A male subject roughly 85 years of age or older, a dermoscopy image of a single skin lesion.
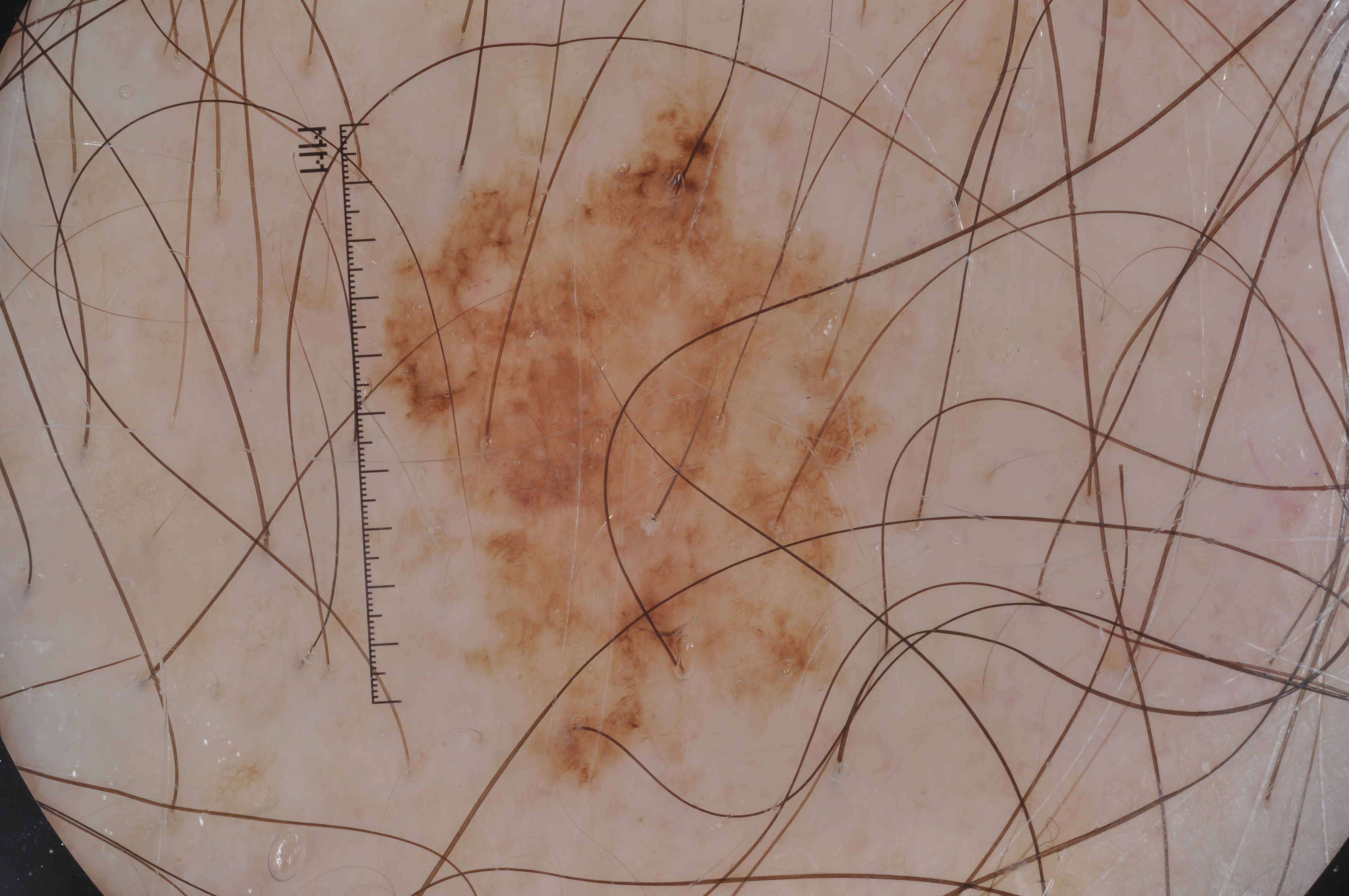<record>
  <dermoscopic_features>
    <present>pigment network</present>
    <absent>negative network, milia-like cysts, streaks</absent>
  </dermoscopic_features>
  <lesion_location>
    <bbox_xyxy>372, 40, 962, 801</bbox_xyxy>
  </lesion_location>
  <diagnosis>
    <name>melanoma</name>
    <malignancy>malignant</malignancy>
    <lineage>melanocytic</lineage>
    <provenance>histopathology</provenance>
  </diagnosis>
</record>